Located on the leg, arm and front of the torso. The photograph is a close-up of the affected area. Texture is reported as raised or bumpy and flat. The patient indicates the condition has been present for less than one week:
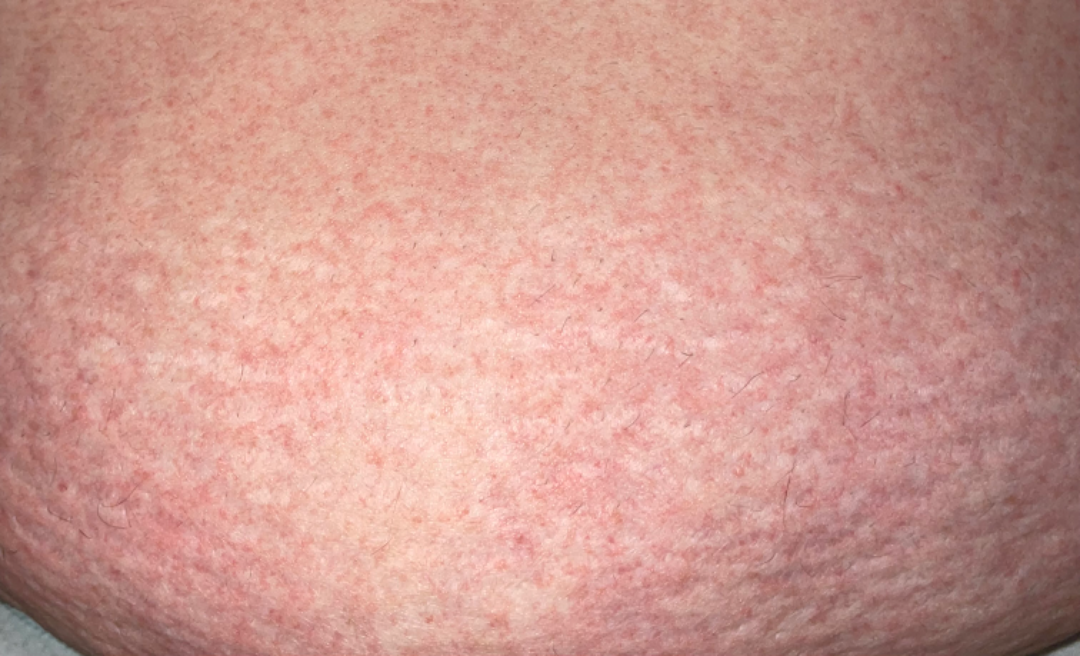assessment: indeterminate from the photograph